A dermoscopy image of a single skin lesion:
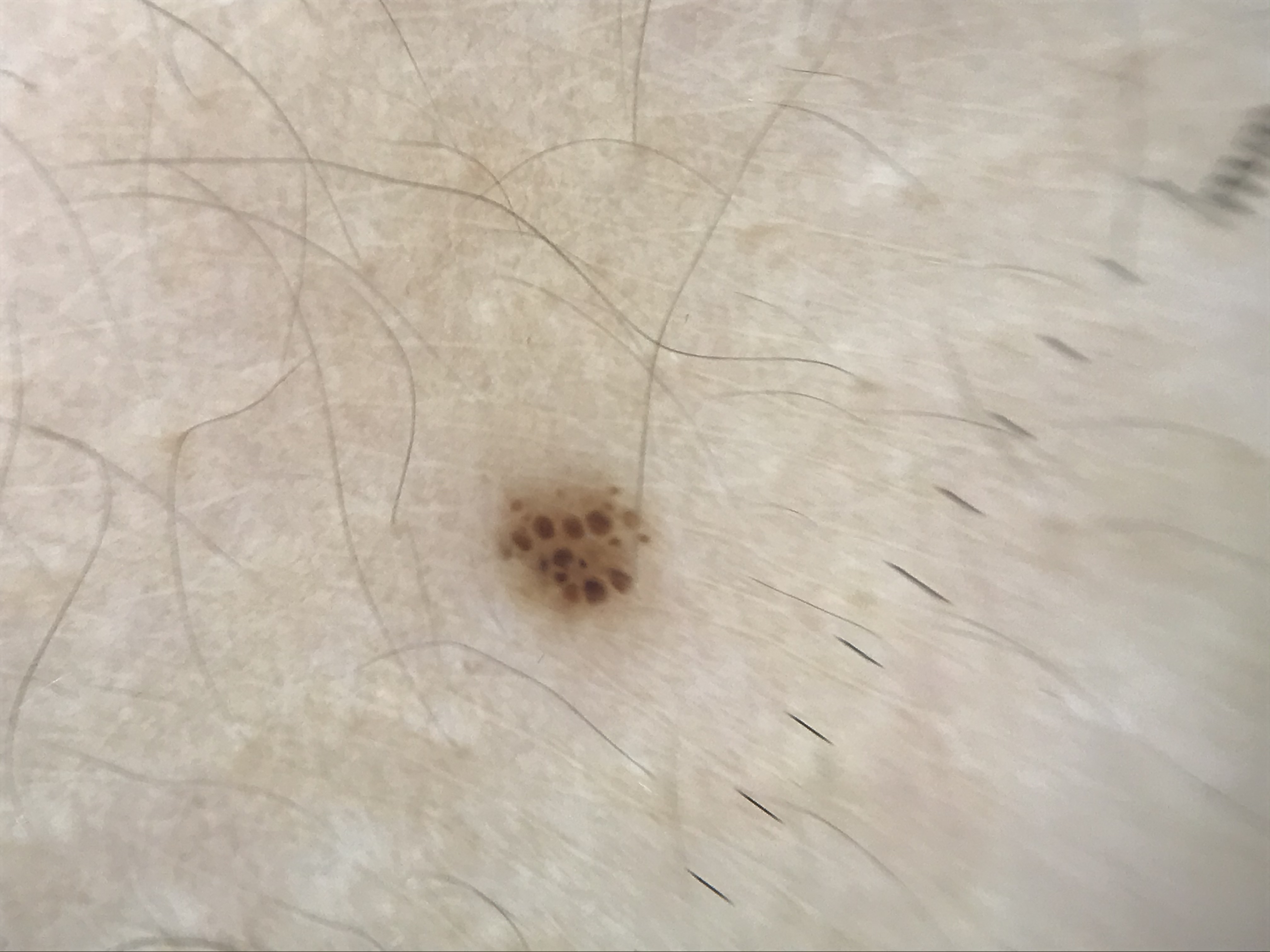Findings:
The architecture is that of a banal lesion.
Conclusion:
Consistent with a junctional nevus.